The patient is female. The photograph was taken at an angle. Texture is reported as flat. The leg and arm are involved: 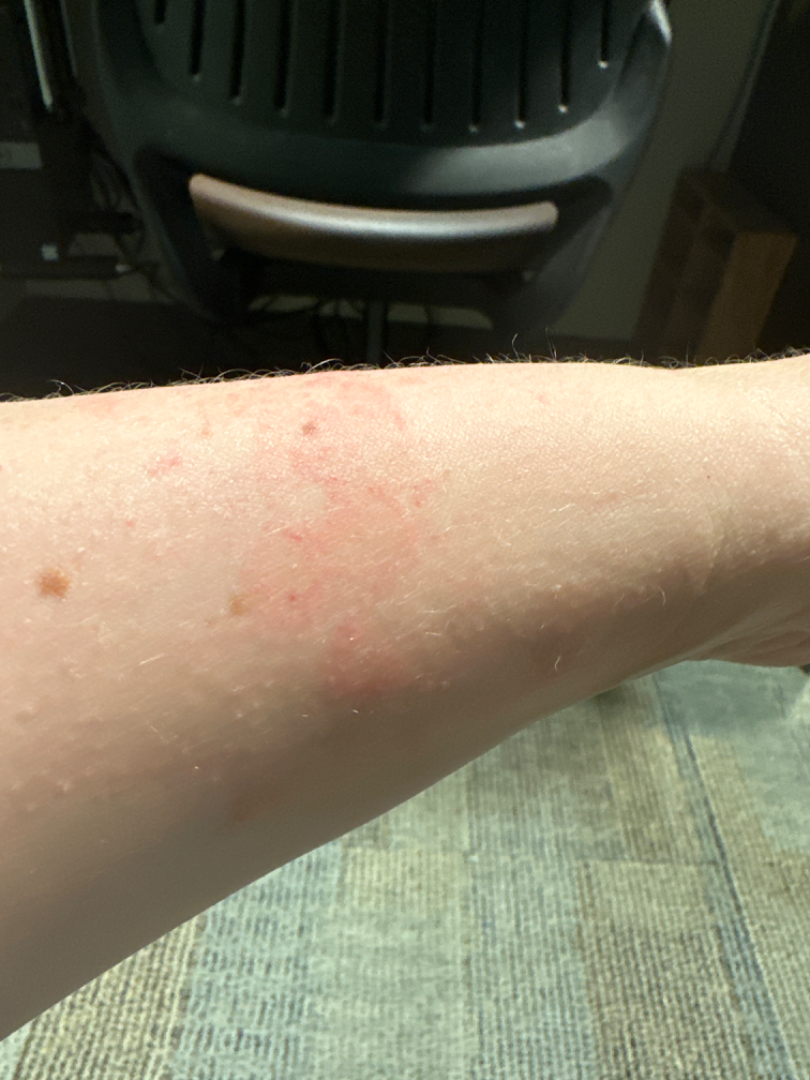Impression: On photographic review: the leading impression is Eczema.